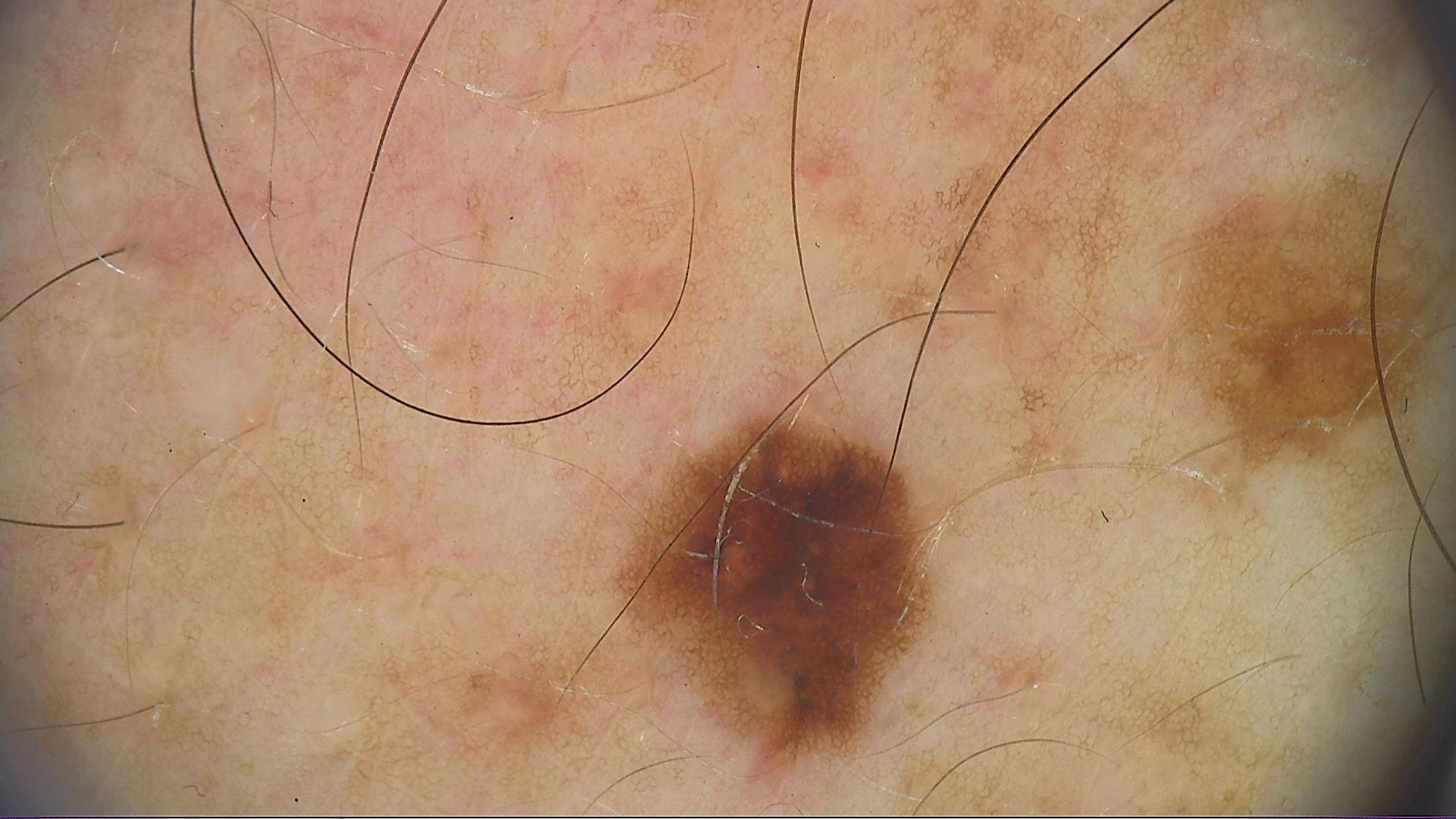Findings:
• image type · dermatoscopy
• diagnostic label · dysplastic junctional nevus (expert consensus)